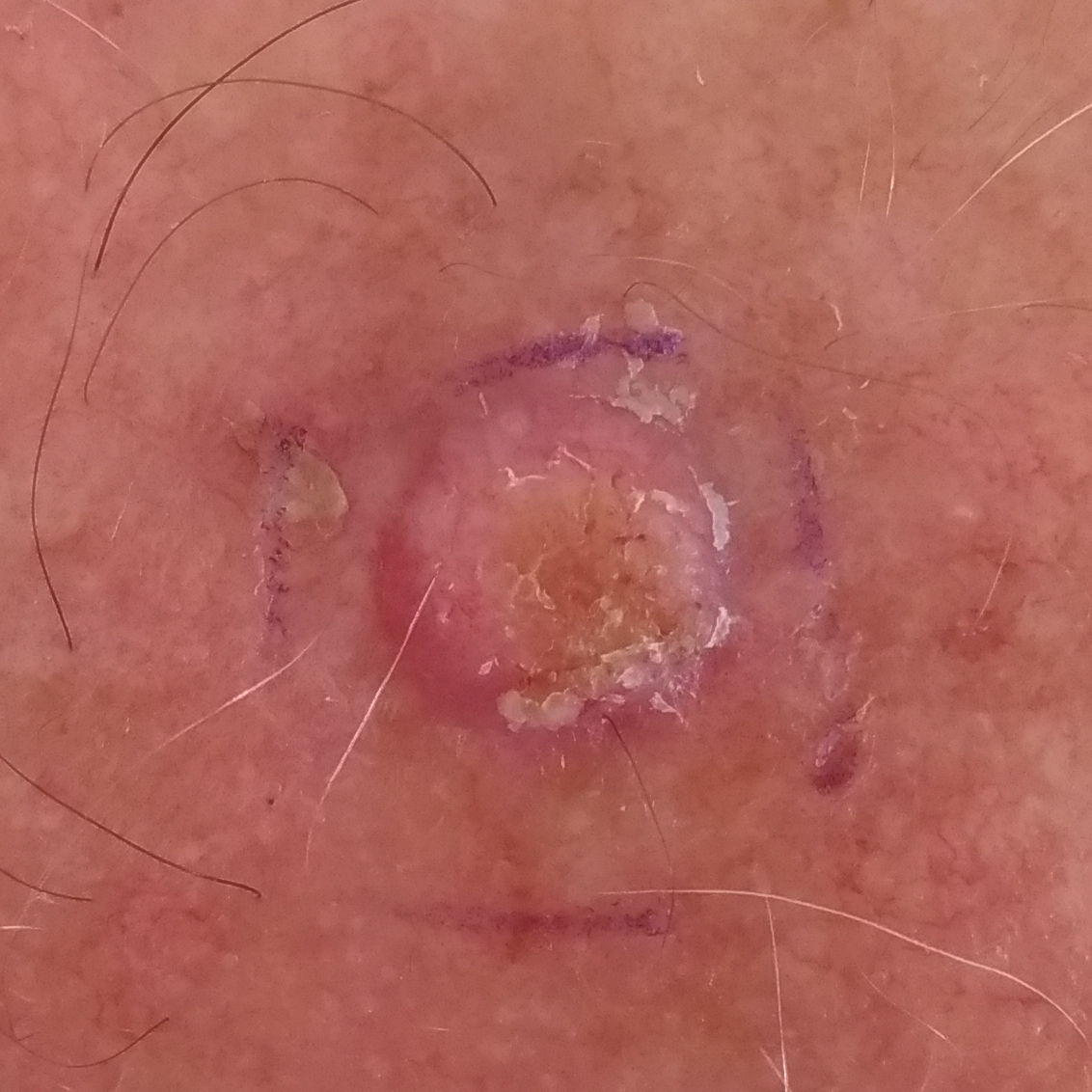Q: What did the workup show?
A: squamous cell carcinoma (biopsy-proven)